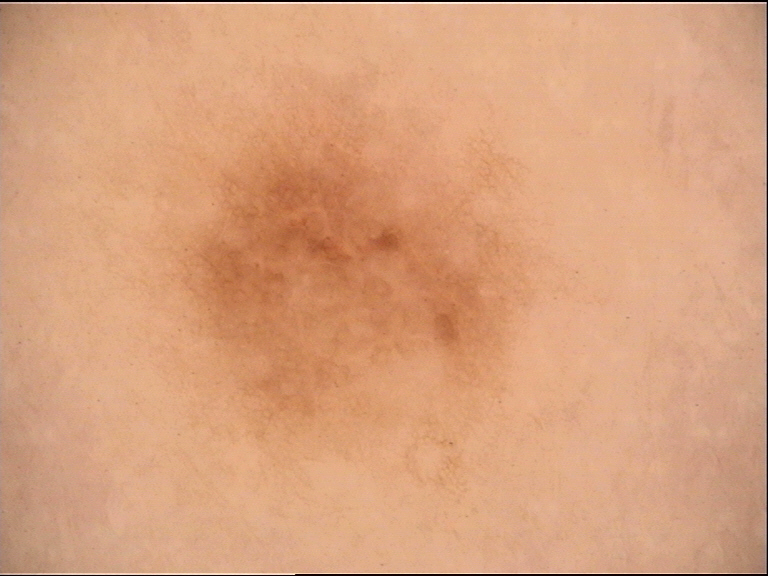Case:
– lesion type — banal
– diagnostic label — junctional nevus (expert consensus)